A dermoscopic close-up of a skin lesion: 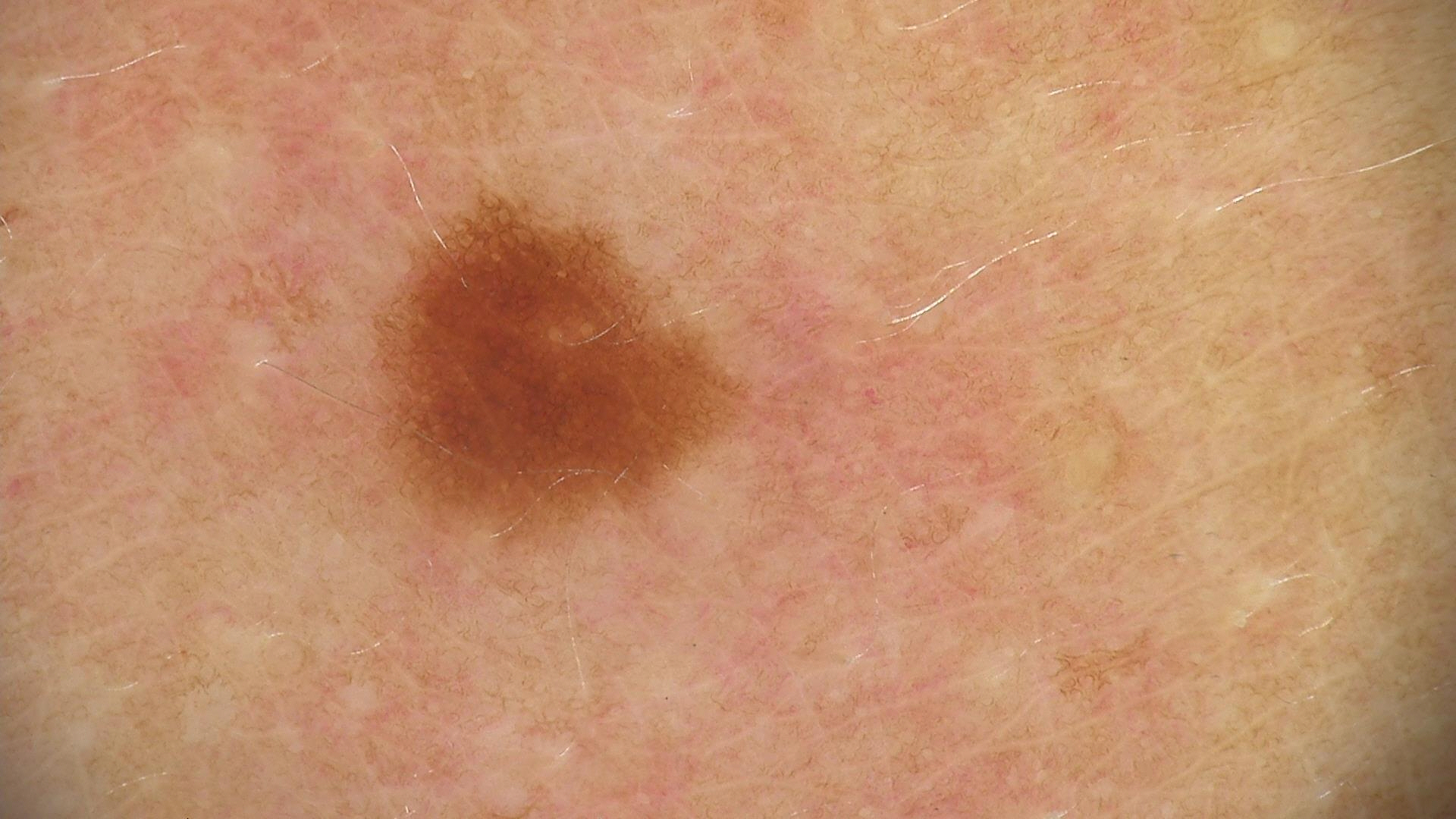Labeled as a dysplastic junctional nevus.